A dermoscopic photograph of a skin lesion:
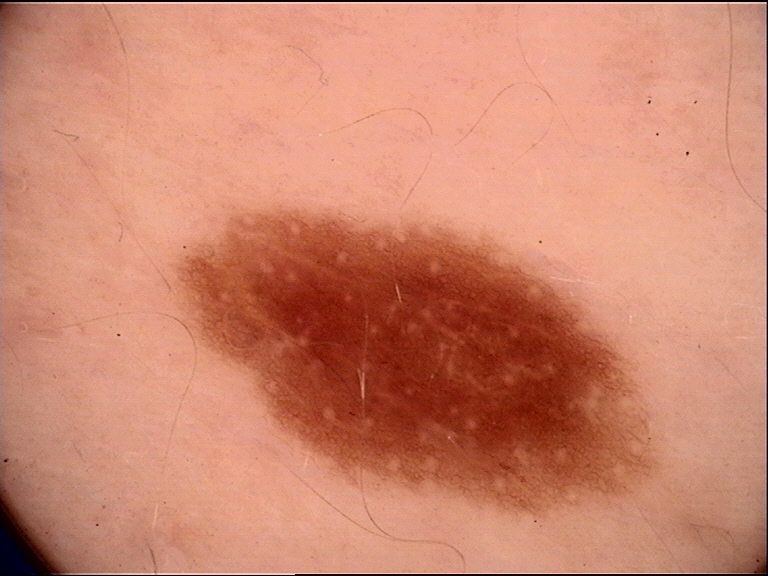Q: What was the diagnostic impression?
A: dysplastic junctional nevus (expert consensus)